This is a dermoscopic photograph of a skin lesion:
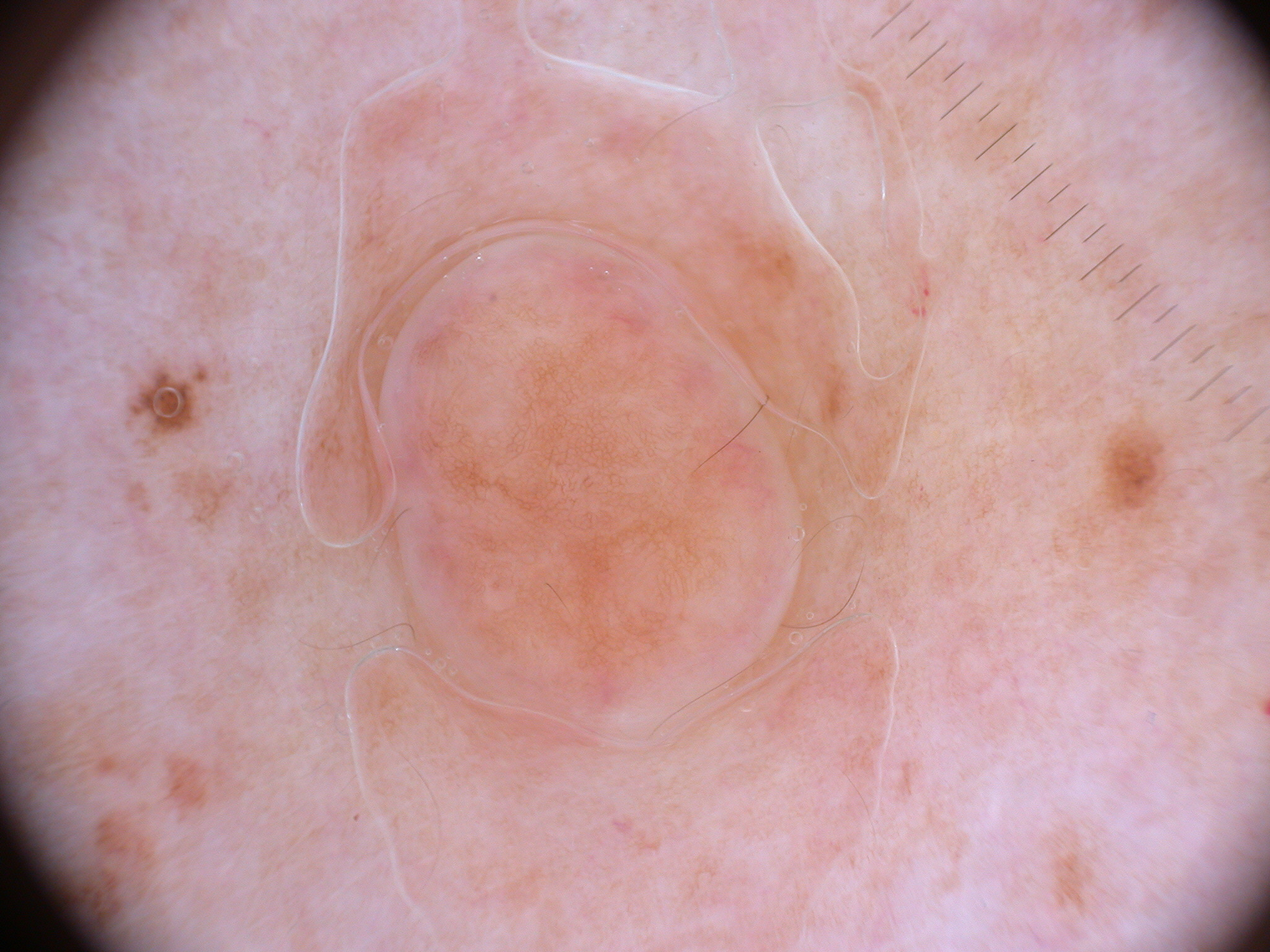Summary: In (x1, y1, x2, y2) order, the lesion's extent is 381, 229, 803, 750. A moderately sized lesion. Dermoscopic review identifies pigment network, with no milia-like cysts, globules, negative network, or streaks. Assessment: Consistent with a melanocytic nevus.